The subject is a female aged 23 to 27. A dermoscopic close-up of a skin lesion.
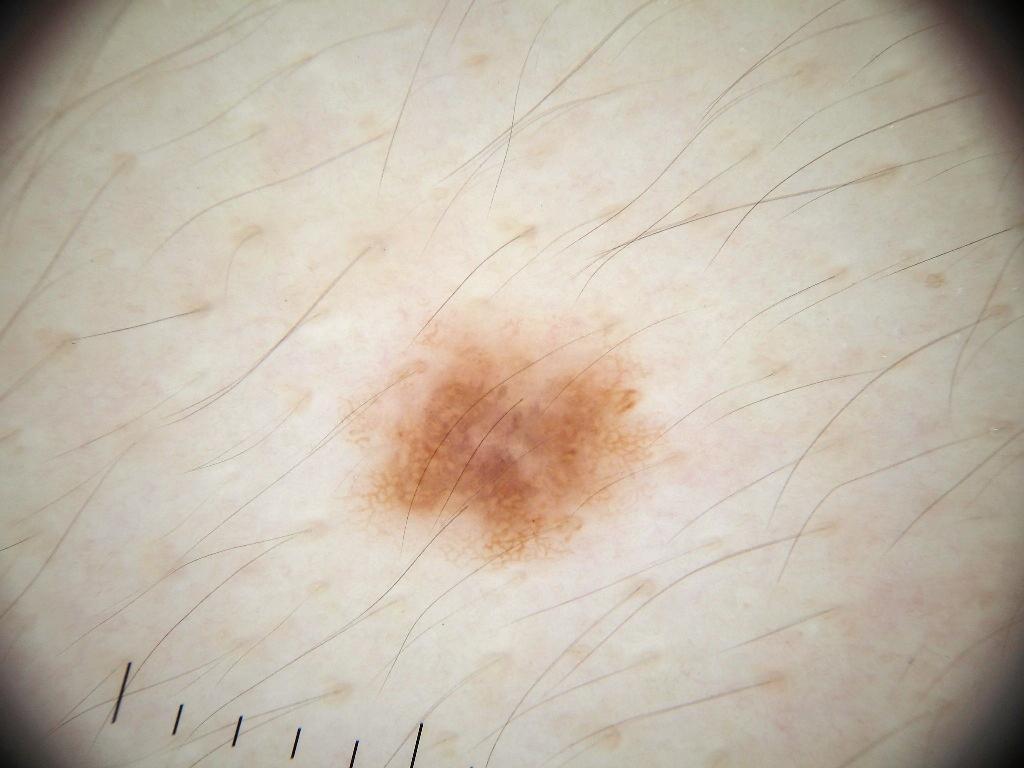Case summary: The lesion occupies roughly 7% of the field. The visible lesion spans x1=347 y1=314 x2=663 y2=568. Dermoscopic review identifies globules, pigment network, and streaks; no negative network or milia-like cysts. Impression: The lesion was assessed as a melanocytic nevus, a benign lesion.